The subject is 40–49, female · the photo was captured at a distance.
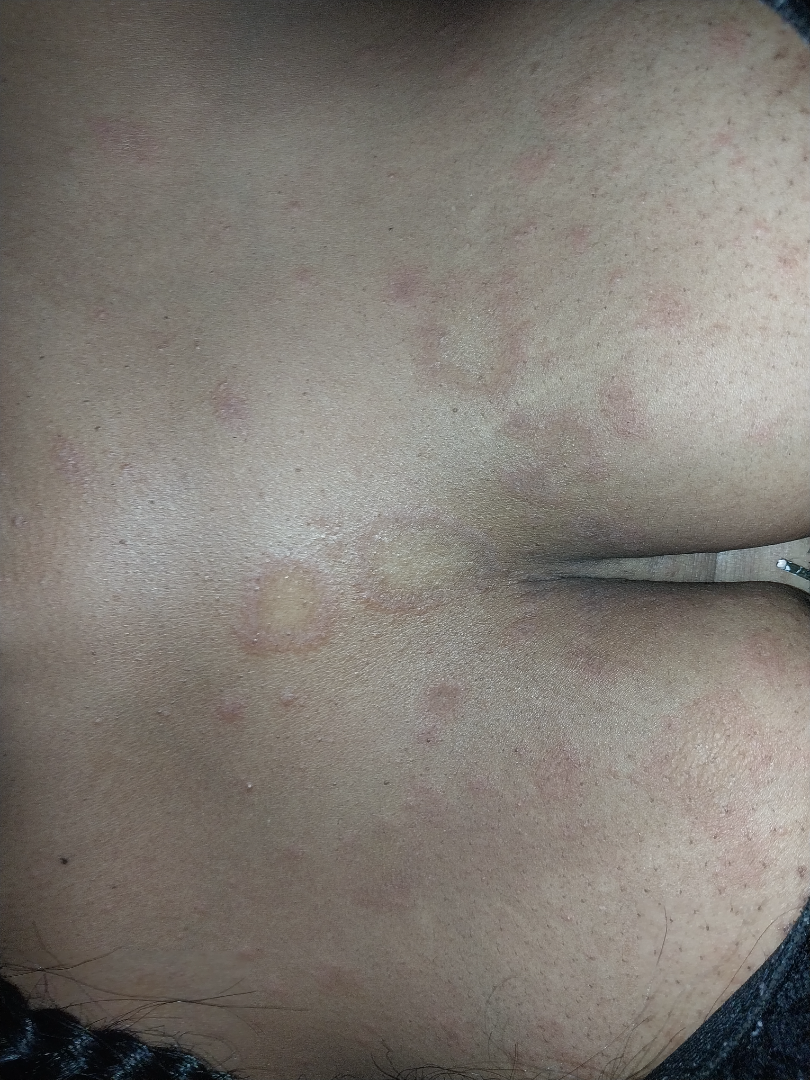Scar Condition (0.35); Pityriasis rosea (0.35); Psoriasis (0.15); Eczema (0.15).